A skin lesion imaged with a dermatoscope — 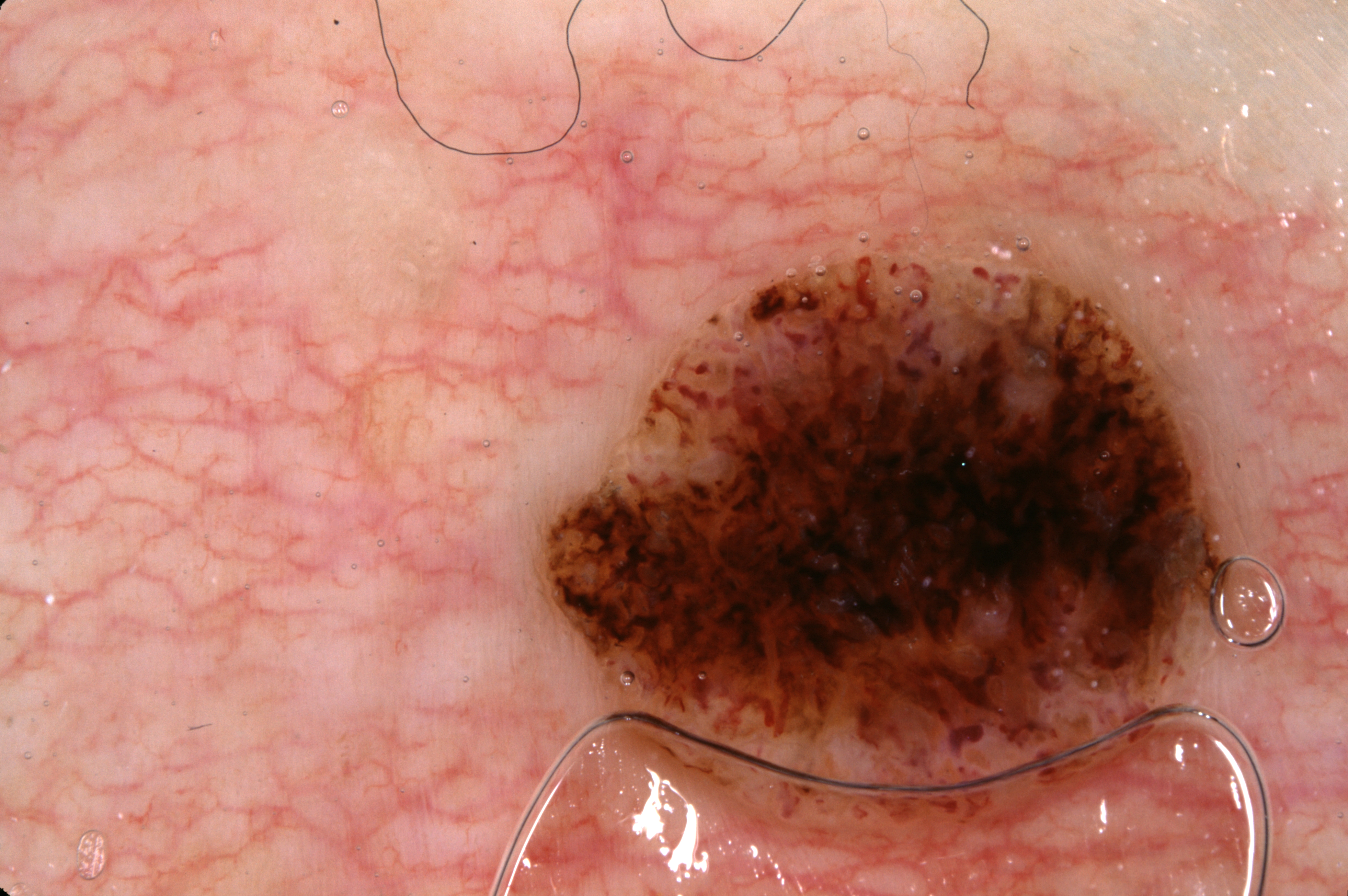Dermoscopy demonstrates no pigment network, streaks, negative network, or milia-like cysts. With coordinates (x1, y1, x2, y2), the lesion is located at [548,259,1242,784]. The diagnostic assessment was a seborrheic keratosis, a benign lesion.